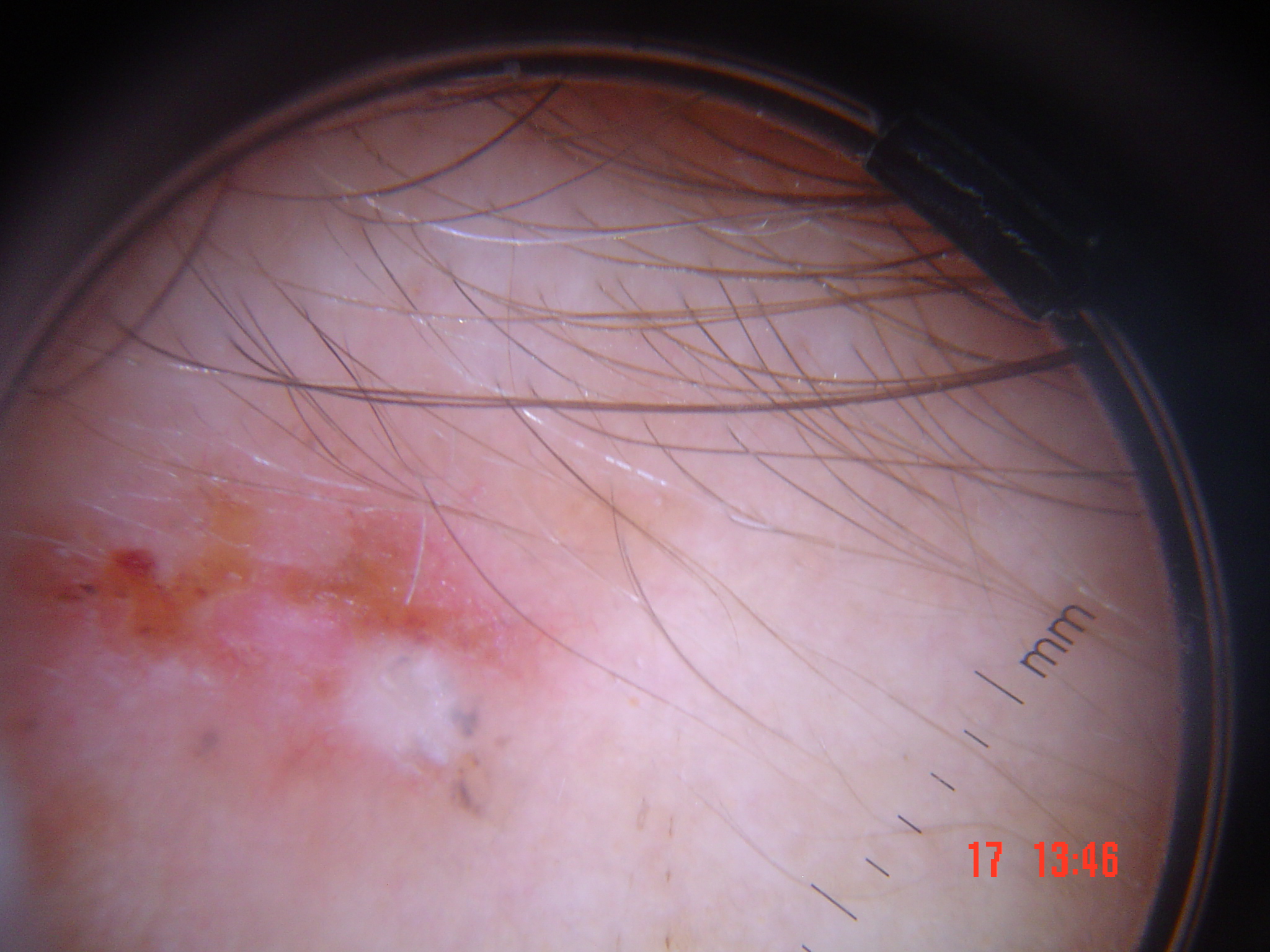lesion type=keratinocytic; label=basal cell carcinoma (biopsy-proven).